The patient says their skin reddens with sun exposure · numerous moles by the patient's own estimate · by self-report, a history of sunbed use · a dermatoscopic image of a skin lesion · imaged for a research study, with no referral diagnosis recorded · a female patient age 26 — 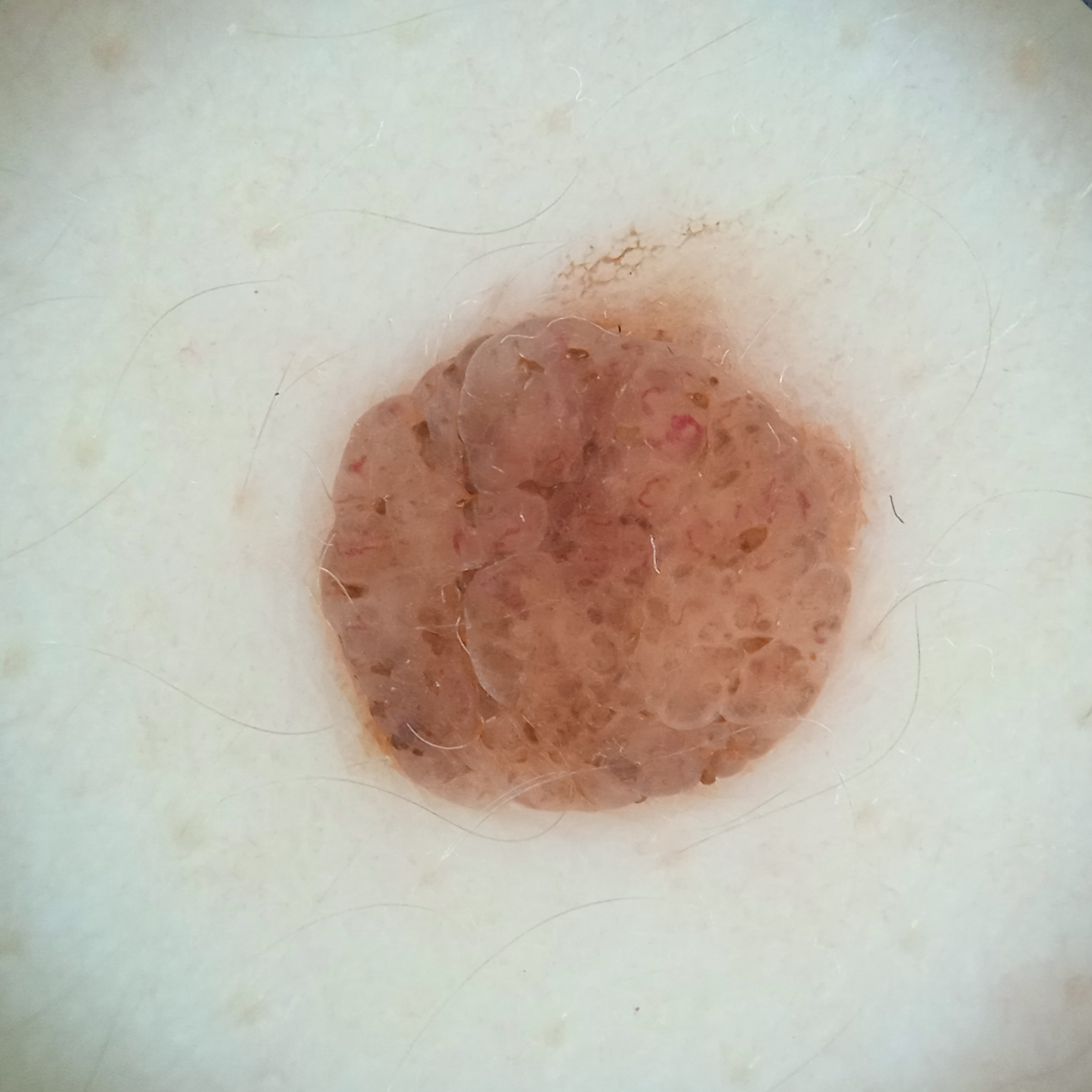{"lesion_location": "the back", "lesion_size": {"diameter_mm": 5.6}, "diagnosis": {"name": "melanocytic nevus", "malignancy": "benign"}}